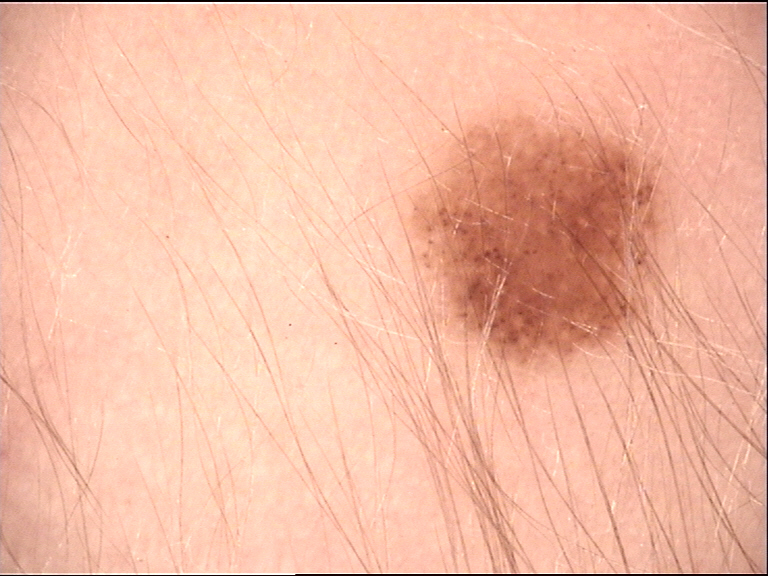The diagnosis was a junctional nevus.